A skin lesion imaged with a dermatoscope:
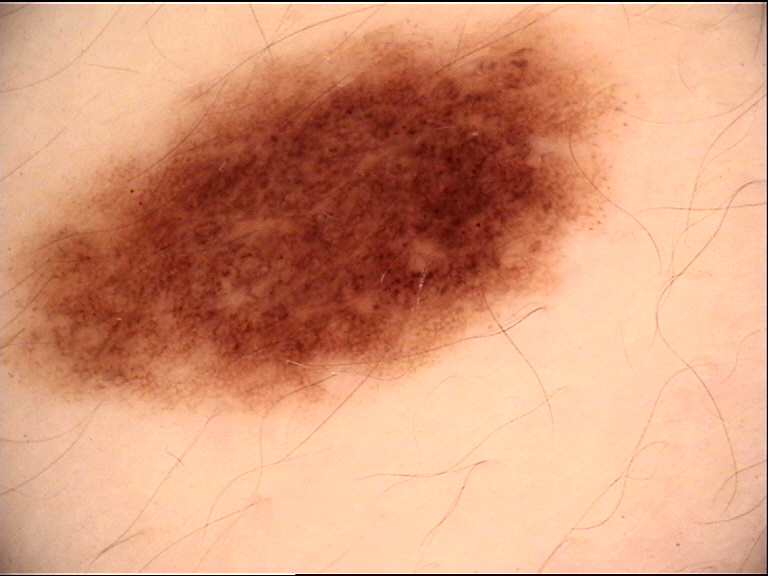Labeled as a dysplastic junctional nevus.